Dermoscopy of a skin lesion.
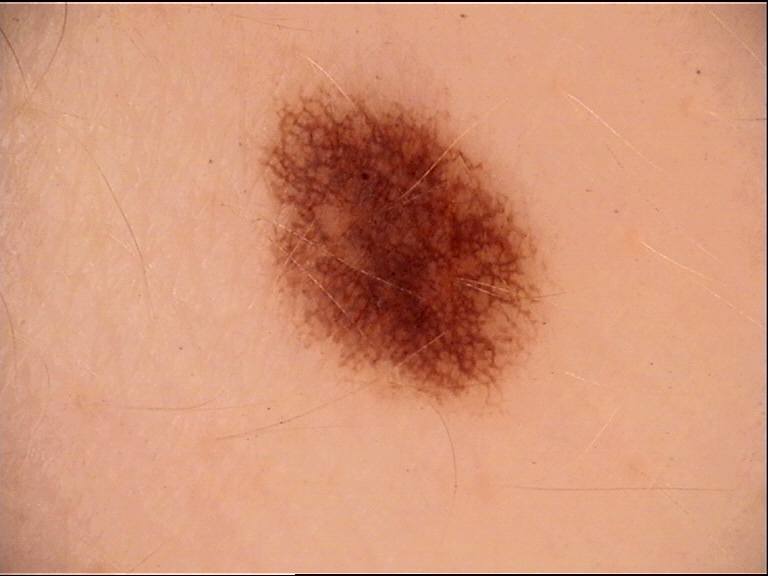Findings:
• diagnostic label · dysplastic junctional nevus (expert consensus)